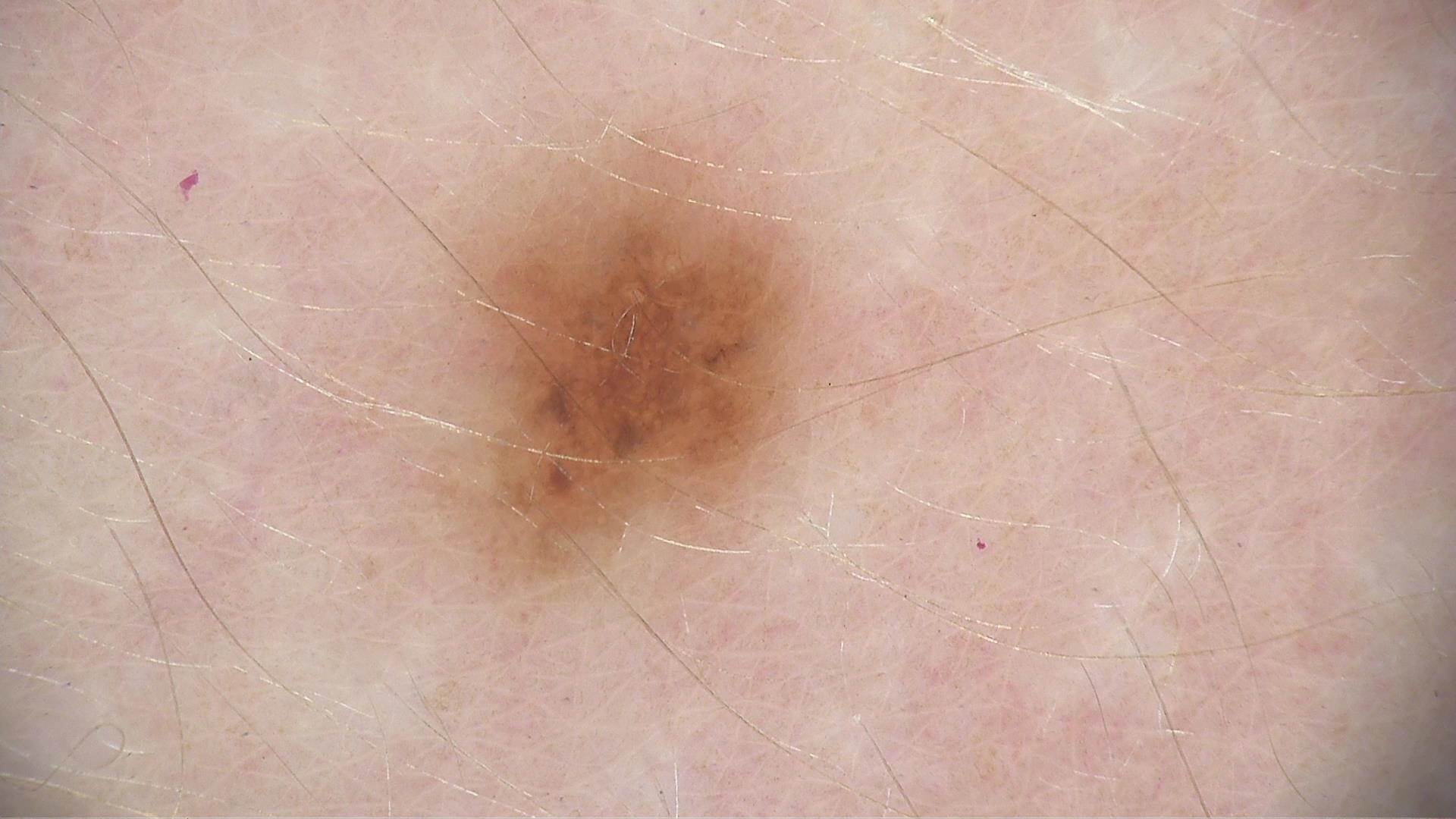– imaging · dermoscopy
– class · dysplastic junctional nevus (expert consensus)